Numerous moles by the patient's own estimate; a male subject age 65; the patient says their skin reddens painfully with sun exposure; the patient reports immunosuppression, a family history of skin cancer, and a personal history of skin cancer; a skin lesion imaged with a dermatoscope:
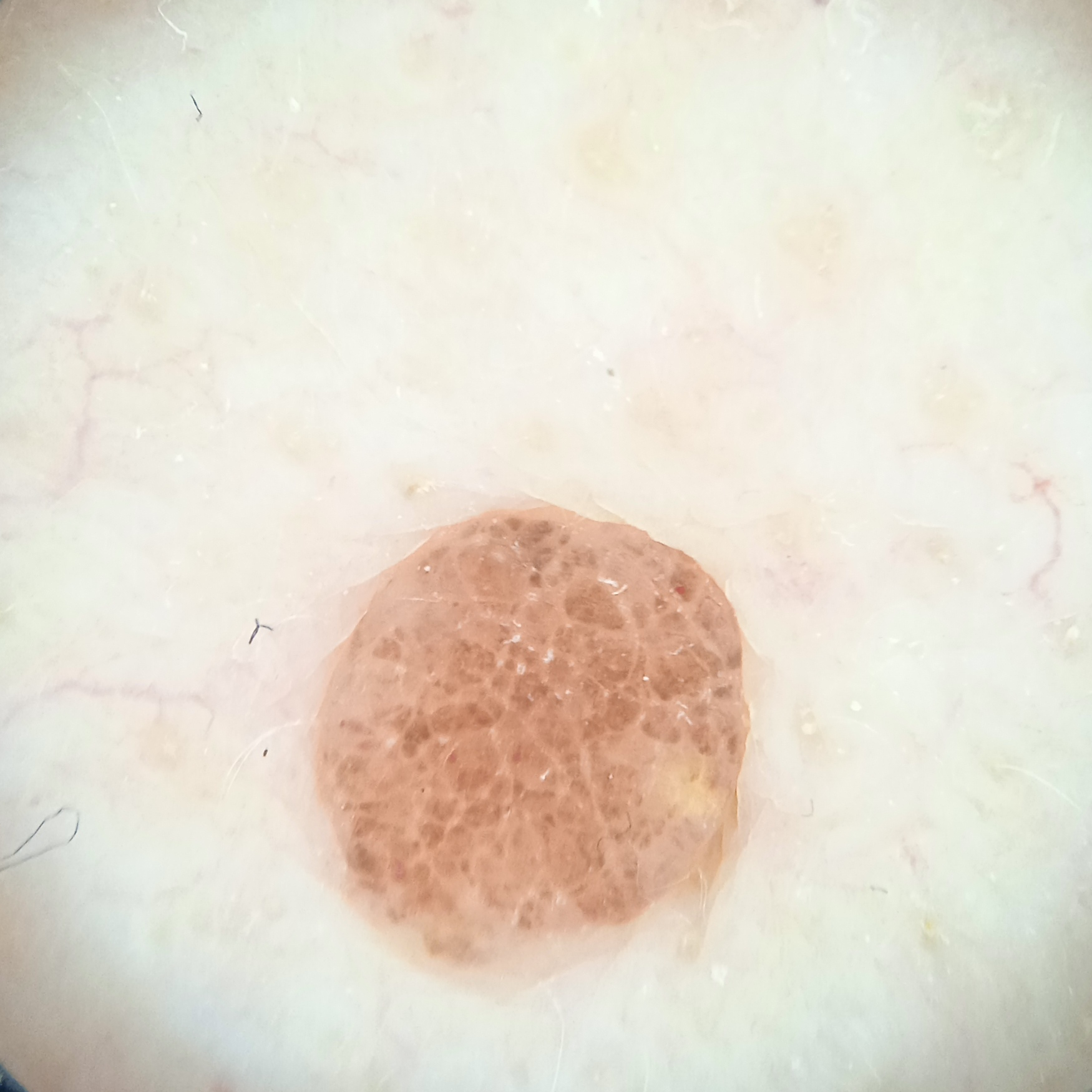Case:
* body site — an arm
* size — 3 mm
* assessment — melanocytic nevus (dermatologist consensus)